The affected area is the arm, palm and front of the torso · the patient is a male aged 30–39 · this image was taken at a distance:
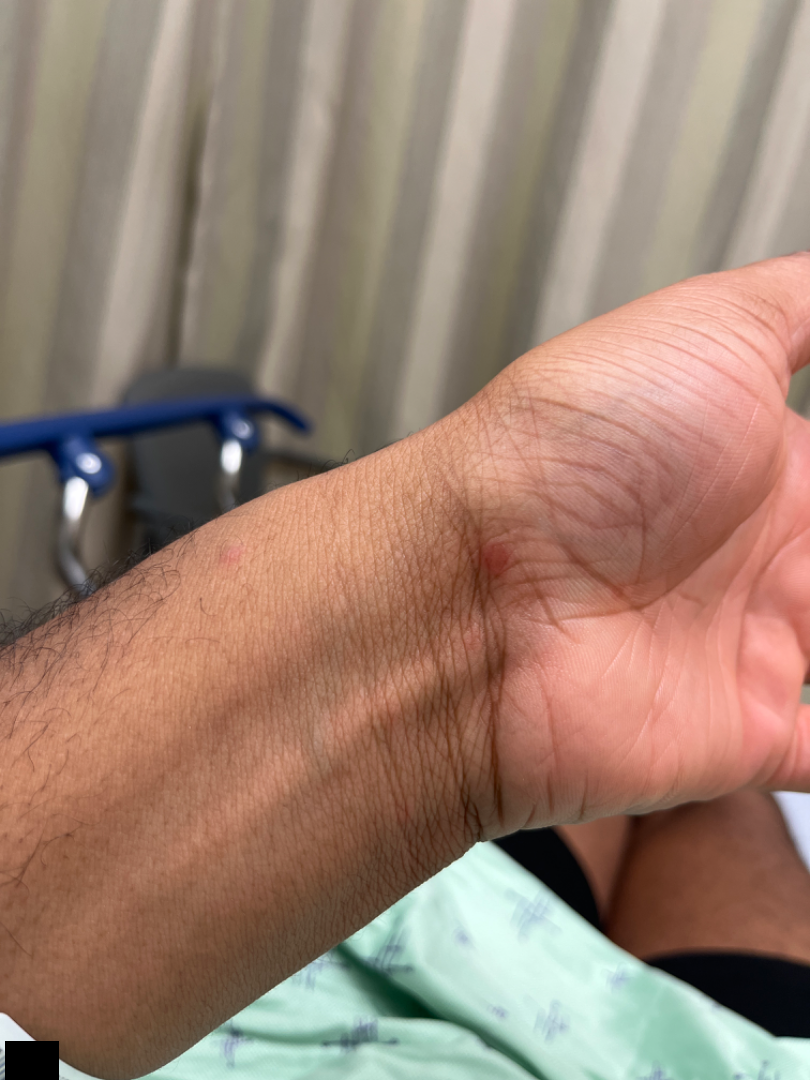The image was not sufficient for the reviewer to characterize the skin condition.